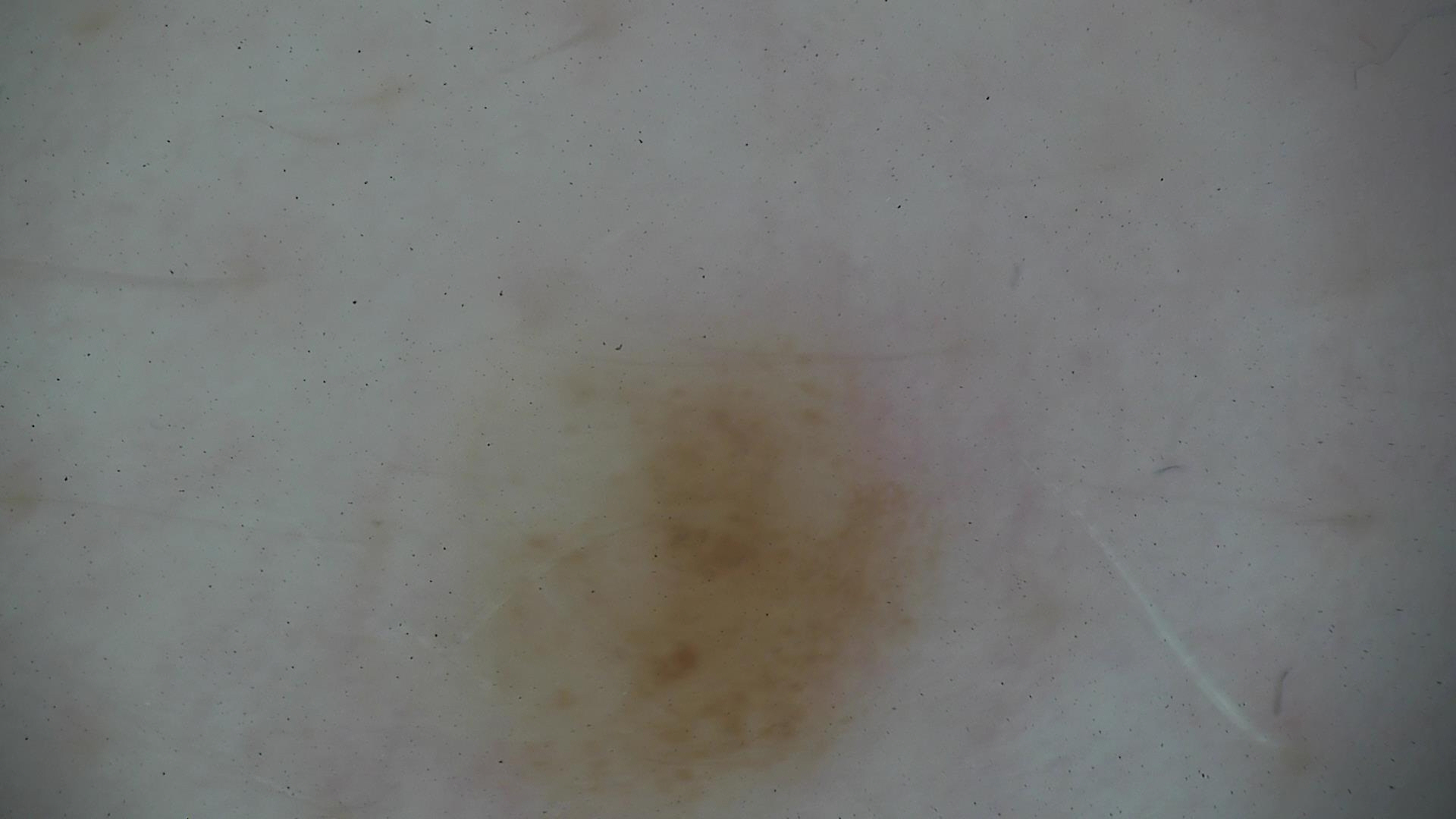The diagnostic label was a dysplastic junctional nevus.